Present for less than one week; Fitzpatrick skin type III; symptoms reported: itching; texture is reported as raised or bumpy; the lesion involves the arm; no relevant systemic symptoms; self-categorized by the patient as a rash; this is a close-up image: 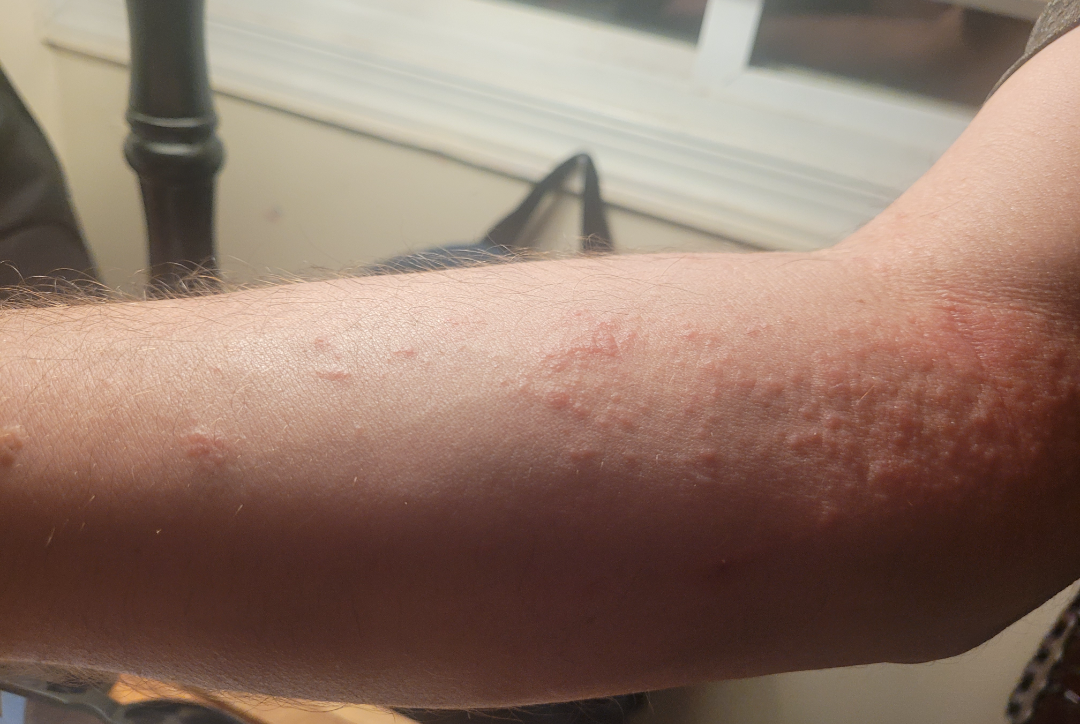Review:
The reviewing dermatologist's impression was: Acute and chronic dermatitis and Allergic Contact Dermatitis were each considered, in no particular order.